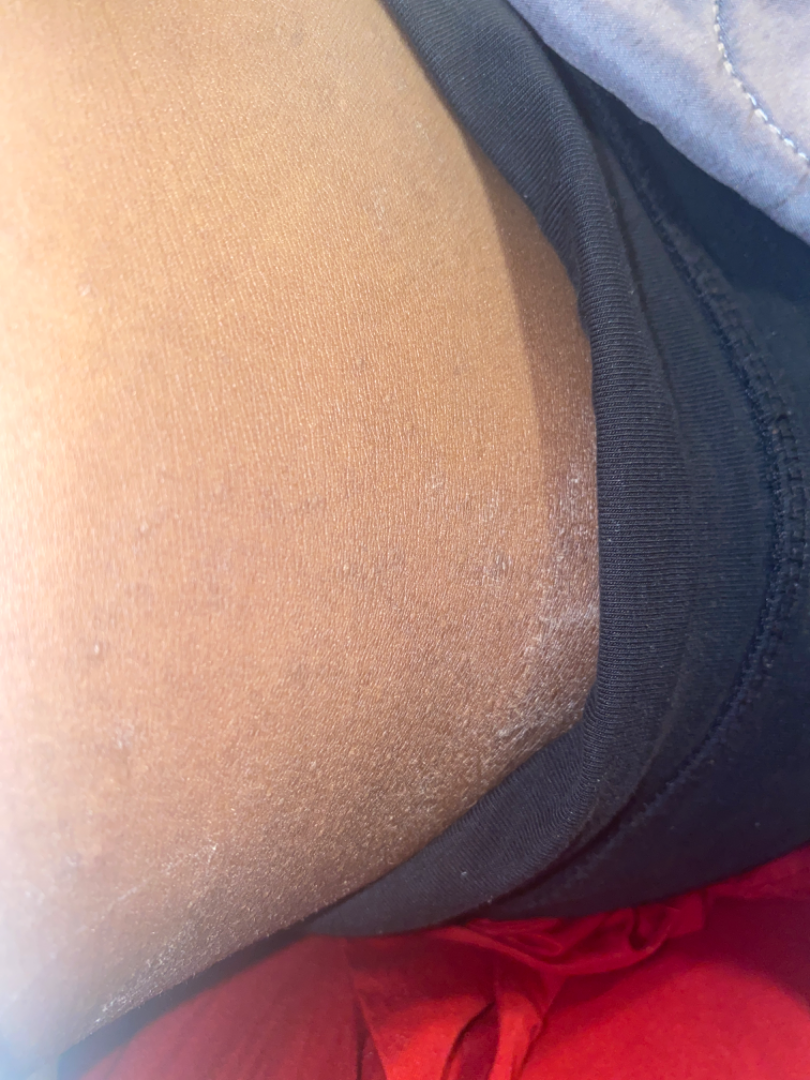The photo was captured at an angle. The patient described the issue as a rash. Texture is reported as flat. No relevant lesion symptoms reported. The patient is 18–29, female. No associated systemic symptoms reported. Xerosis and Eczema were considered with similar weight.